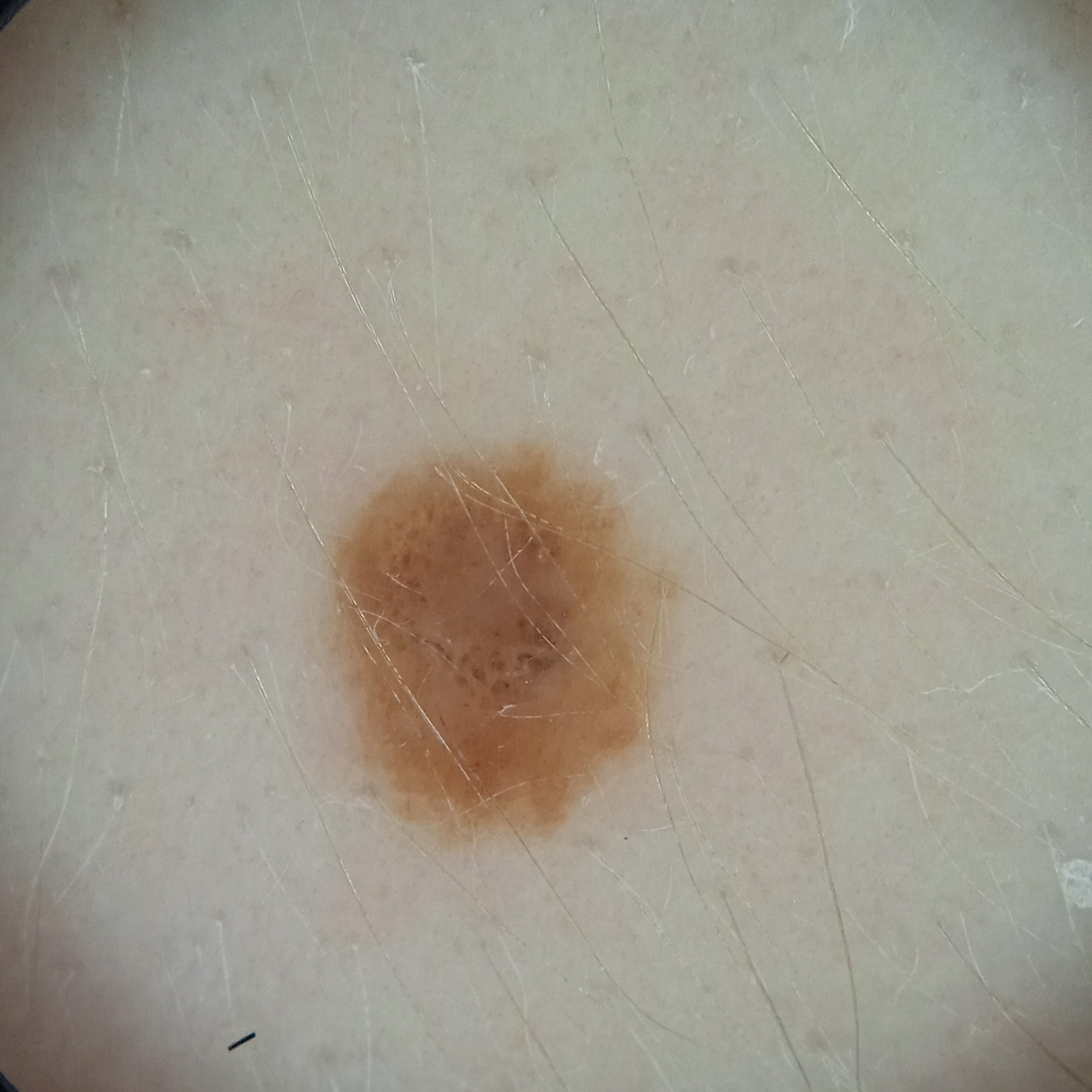mole_burden: a moderate number of melanocytic nevi
patient:
  age: 27
  sex: female
image: dermoscopic image
sun_reaction: skin reddens with sun exposure
referral: research study (no referral diagnosis)
lesion_location: the torso
lesion_size:
  diameter_mm: 4.4
diagnosis:
  name: melanocytic nevus
  malignancy: benign